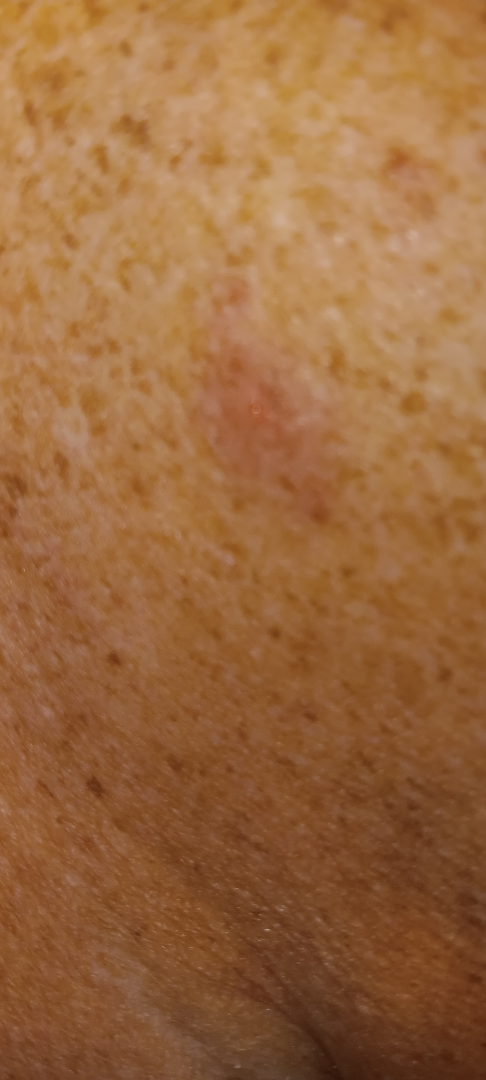<report>
  <assessment>could not be assessed</assessment>
  <patient>female, age 60–69</patient>
  <shot_type>close-up</shot_type>
  <body_site>arm</body_site>
</report>